A dermoscopic image of a skin lesion.
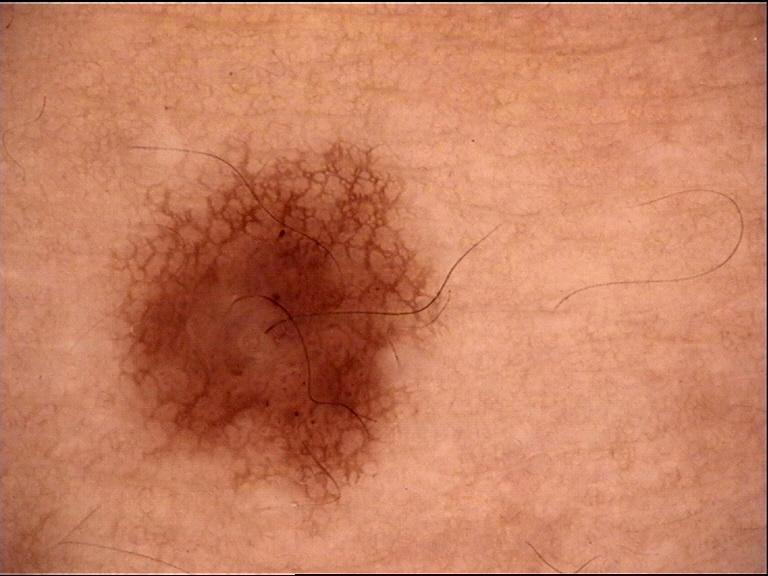Impression: Diagnosed as a benign lesion — a dysplastic junctional nevus.